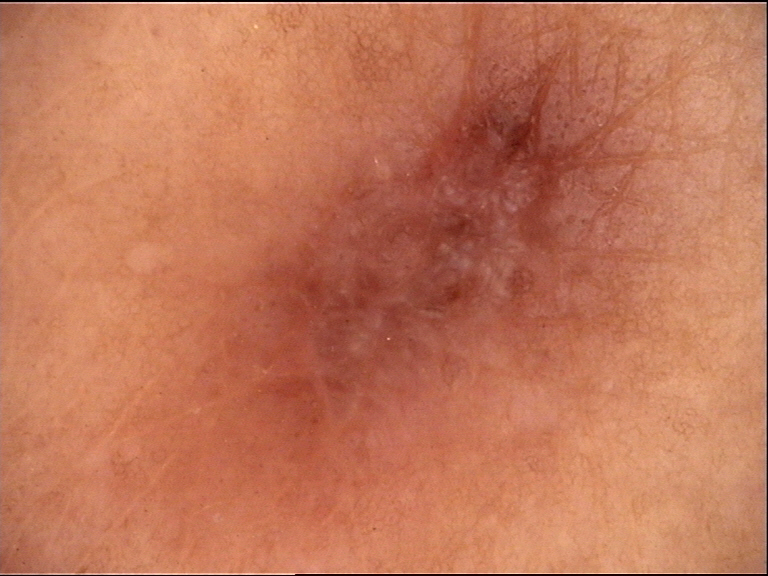{"lesion_type": {"main_class": "fibro-histiocytic"}, "diagnosis": {"name": "dermatofibroma", "code": "df", "malignancy": "benign", "super_class": "non-melanocytic", "confirmation": "expert consensus"}}